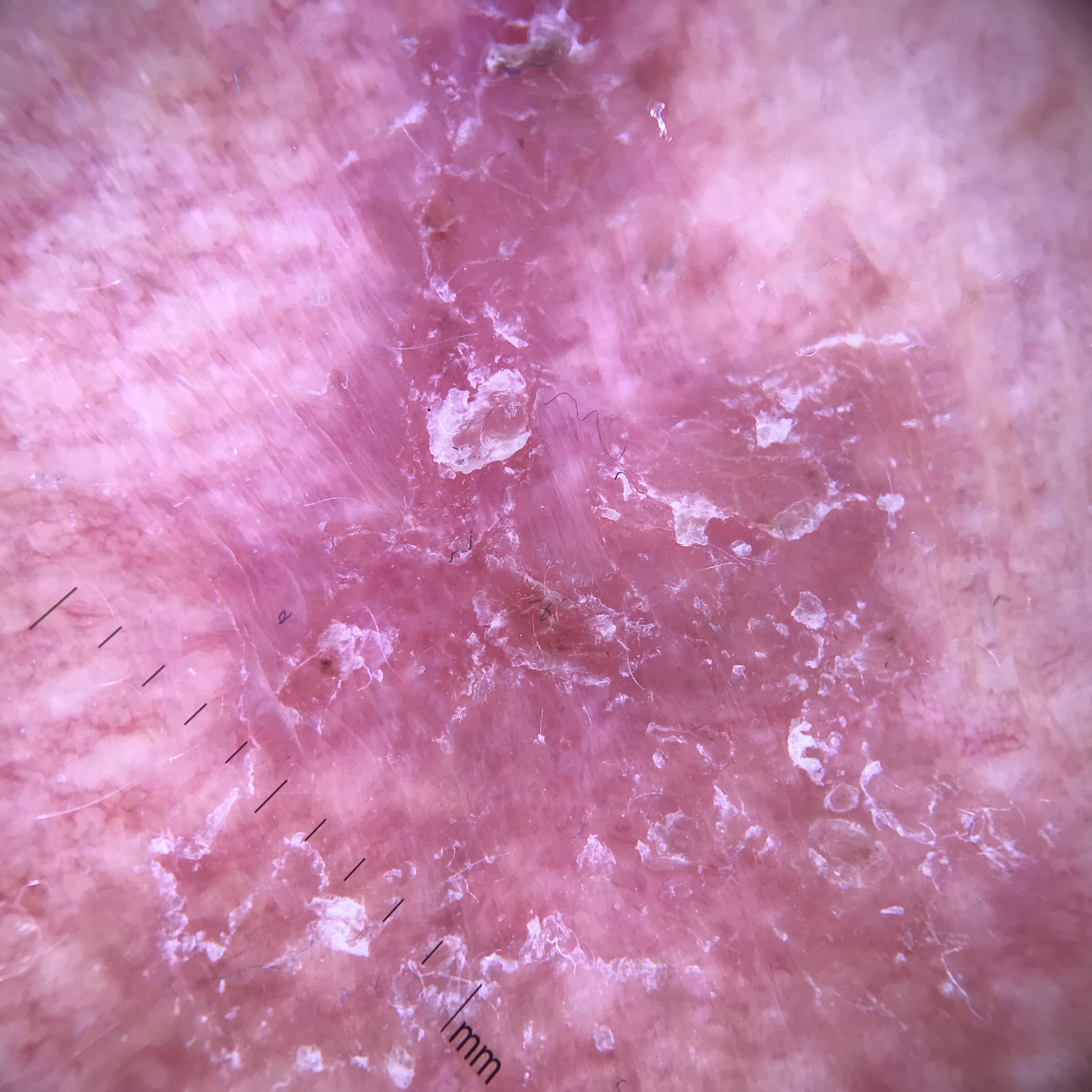Case:
A dermoscopic close-up of a skin lesion. This is a keratinocytic lesion.
Conclusion:
Histopathology confirmed a skin cancer — Bowen's disease.